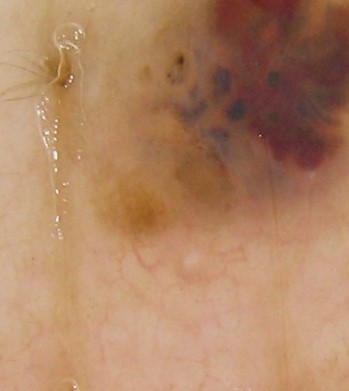Case:
A dermoscopic close-up of a skin lesion. The morphology is that of a keratinocytic lesion.
Conclusion:
Confirmed on histopathology as a basal cell carcinoma.